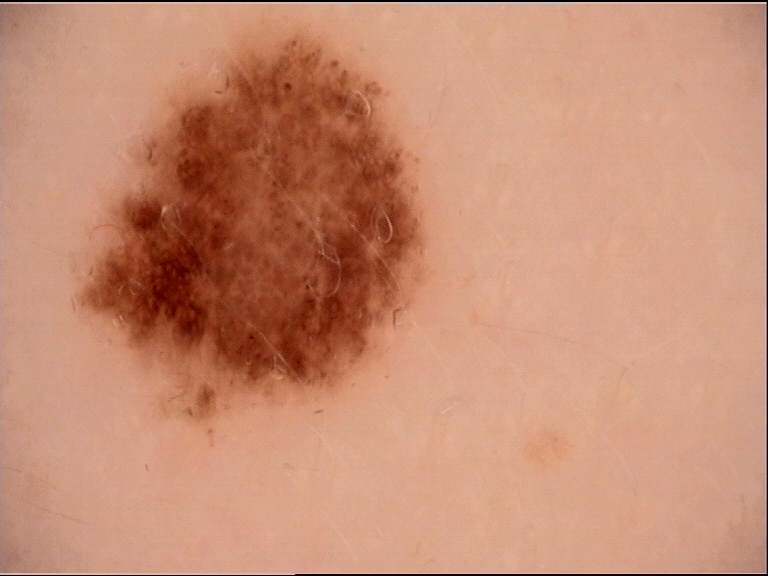Case: A dermoscopic photograph of a skin lesion. Conclusion: Diagnosed as a benign lesion — a dysplastic junctional nevus.